A female subject in their mid- to late 80s or older; an overview clinical photograph of a skin lesion: 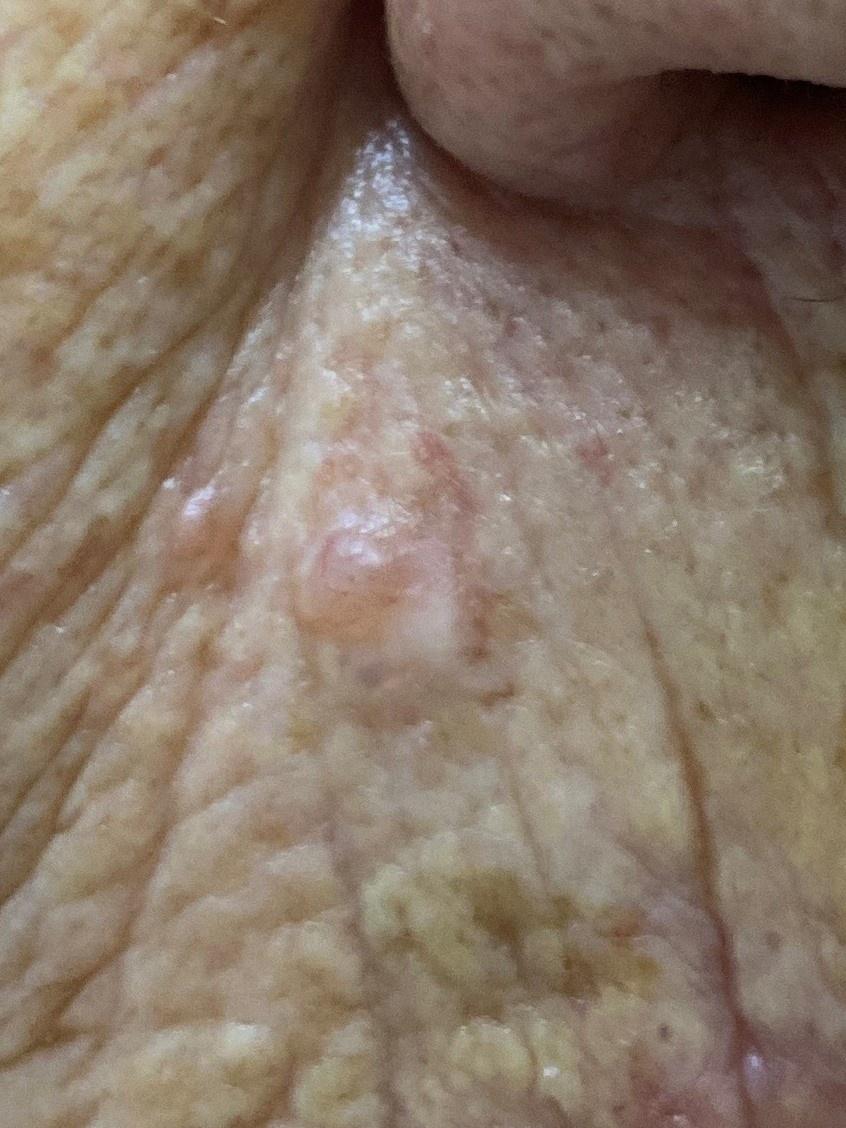<skin_lesion>
<lesion_location>
<region>the head or neck</region>
</lesion_location>
<diagnosis>
<name>Basal cell carcinoma</name>
<malignancy>malignant</malignancy>
<confirmation>histopathology</confirmation>
<lineage>adnexal</lineage>
</diagnosis>
</skin_lesion>